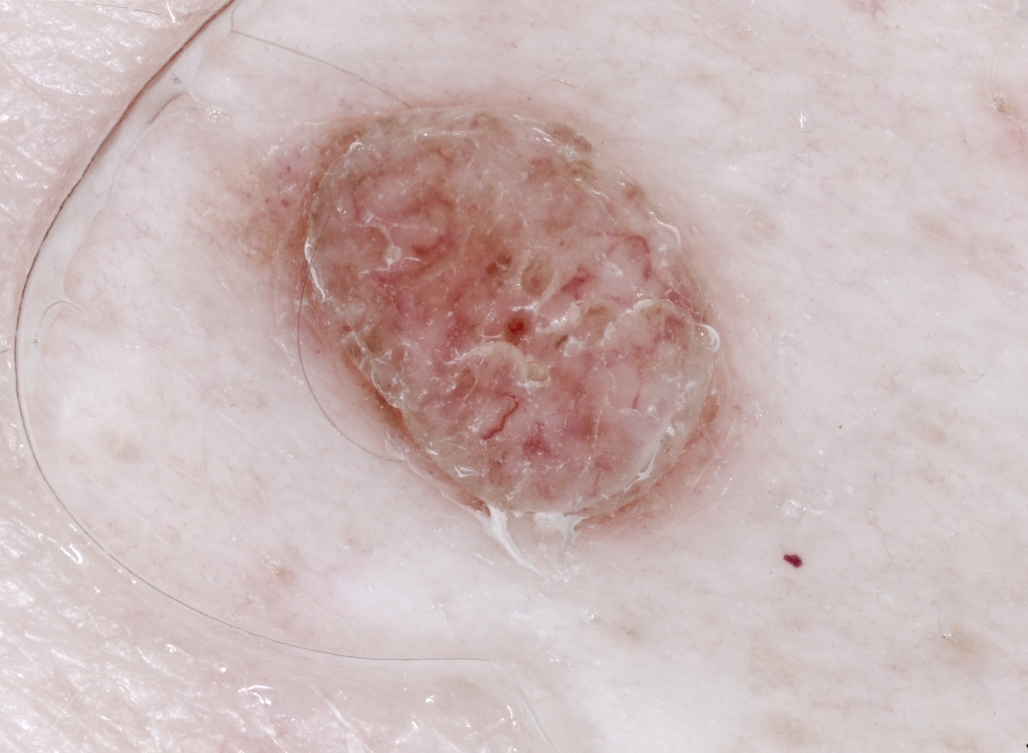{"image": {"modality": "dermoscopy"}, "patient": {"sex": "male", "age_approx": 65}, "dermoscopic_features": {"present": [], "absent": ["streaks", "milia-like cysts", "pigment network", "negative network"]}, "lesion_extent": {"approx_field_fraction_pct": 20}, "lesion_location": {"bbox_xyxy": [227, 91, 742, 540]}, "diagnosis": {"name": "melanocytic nevus", "malignancy": "benign", "lineage": "melanocytic", "provenance": "clinical"}}